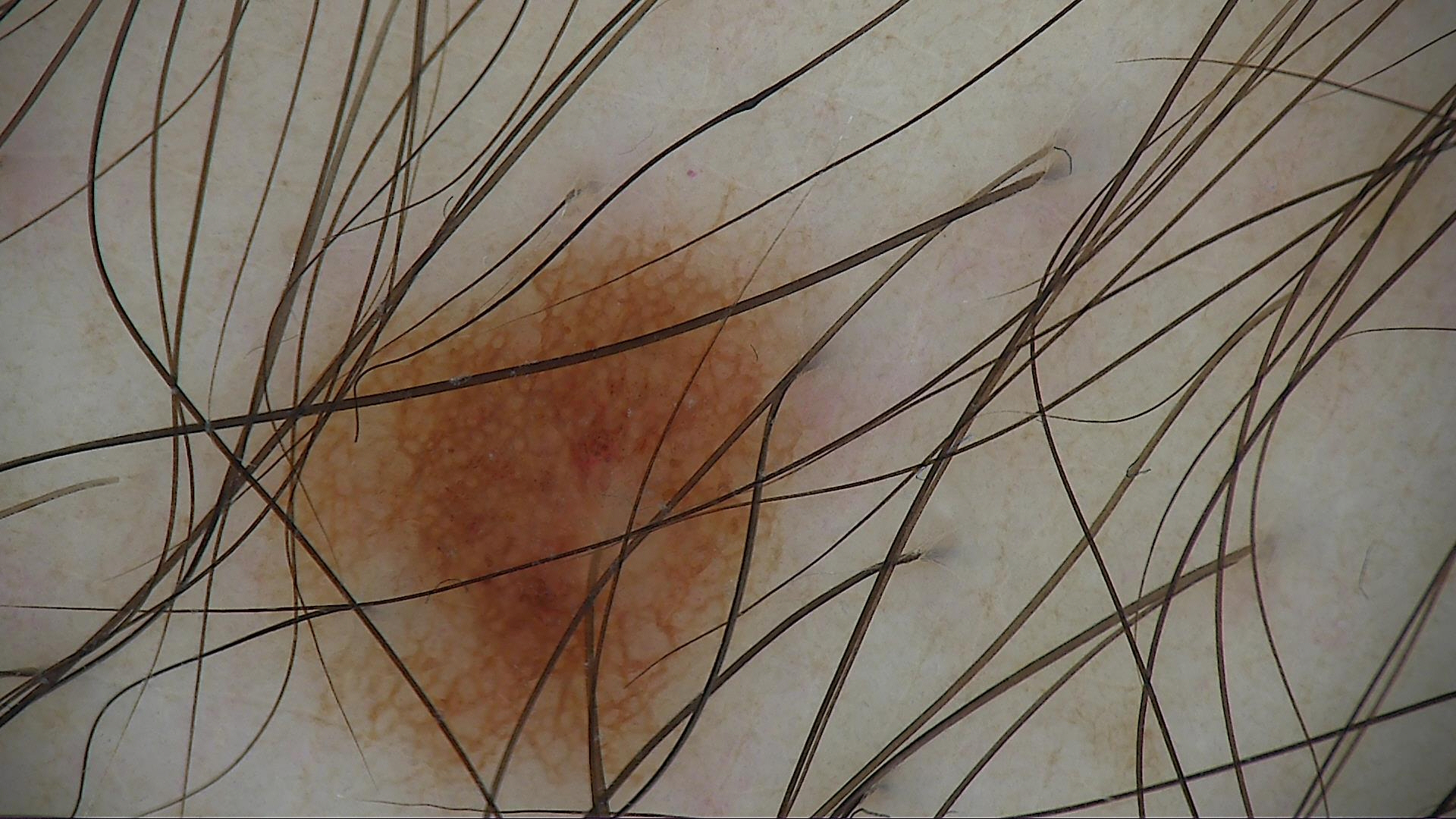image = dermoscopy
classification = banal
assessment = junctional nevus (expert consensus)